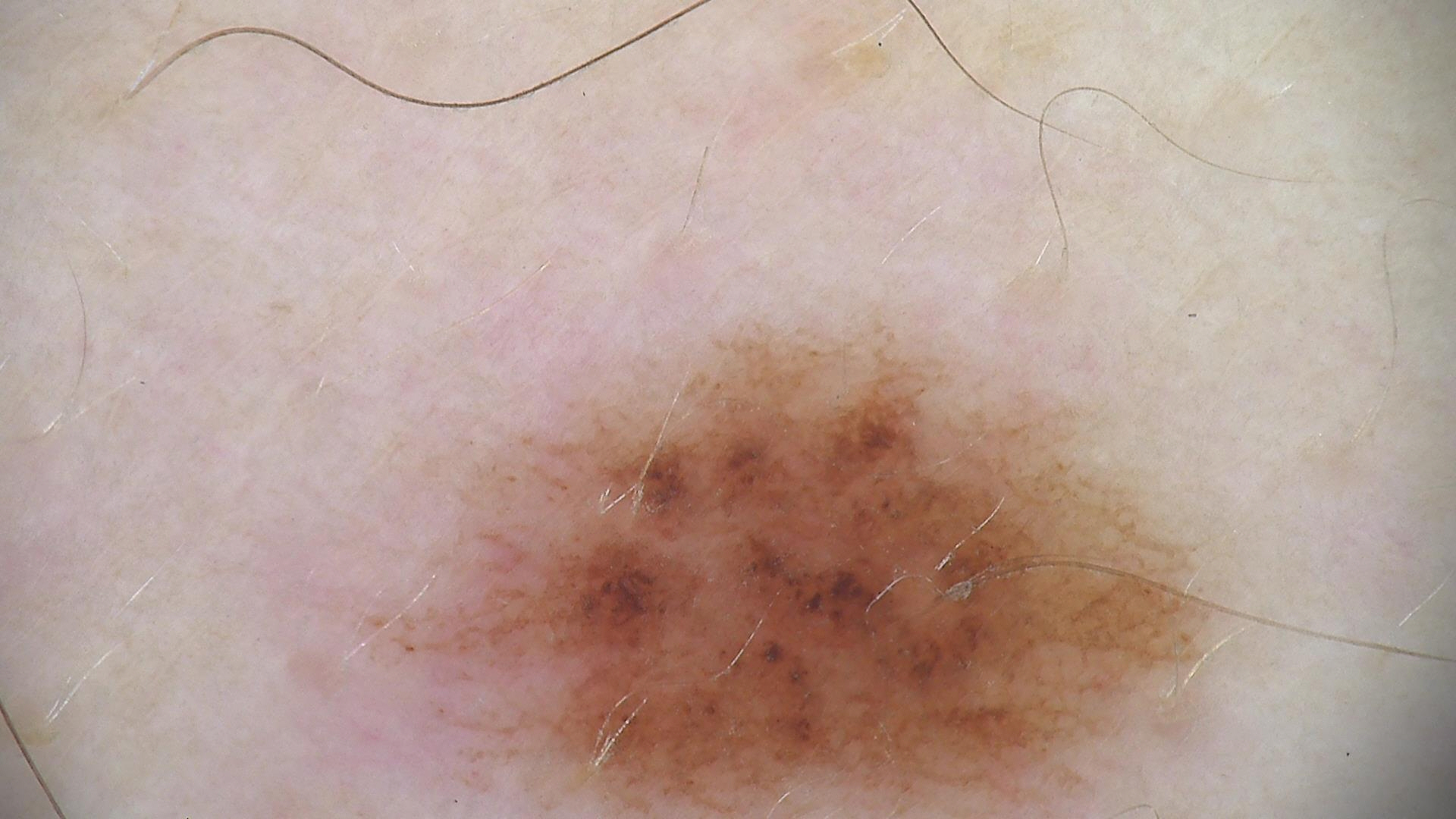Consistent with a benign lesion — a dysplastic junctional nevus.